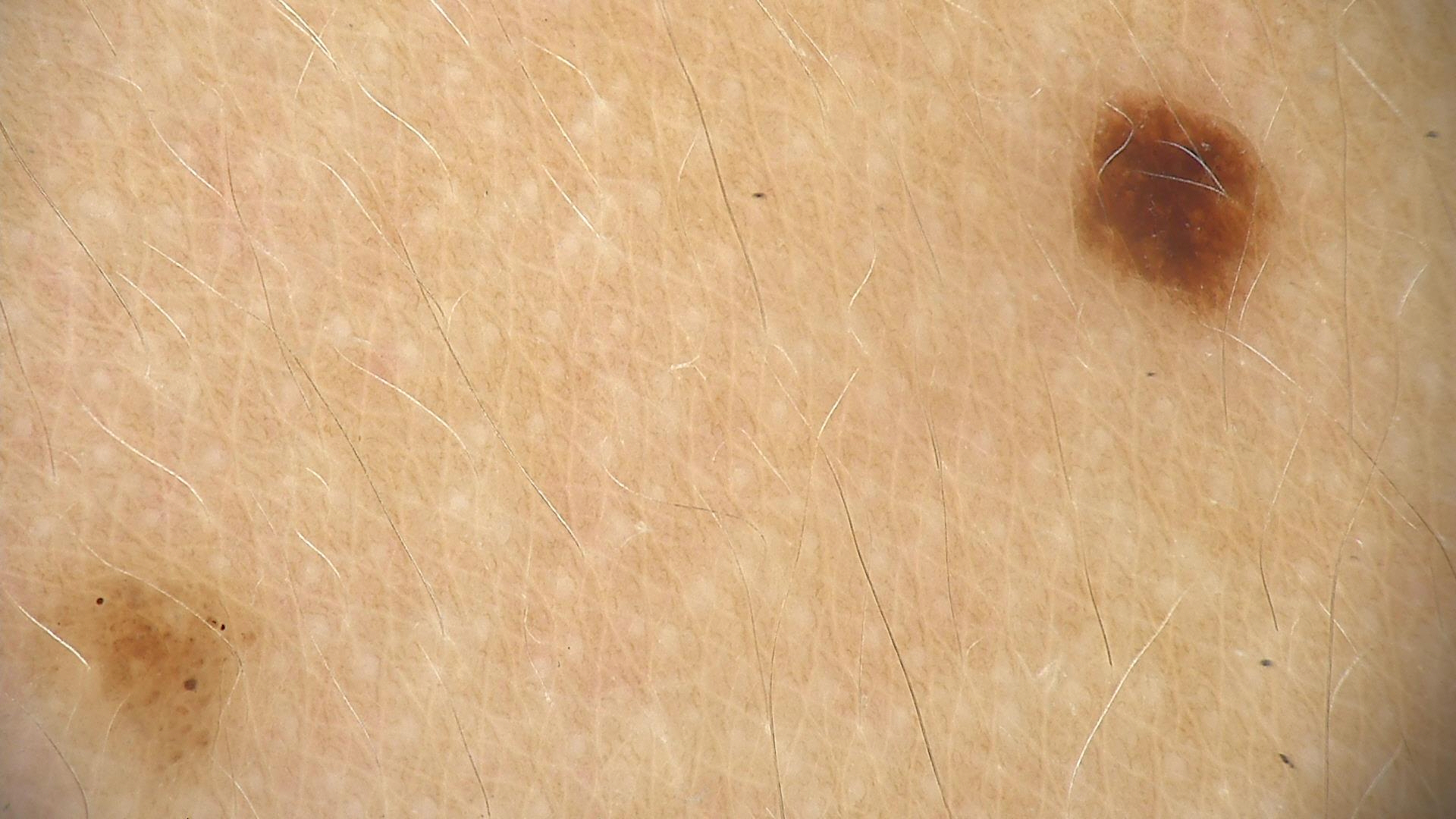The diagnostic label was a benign lesion — a dysplastic junctional nevus.